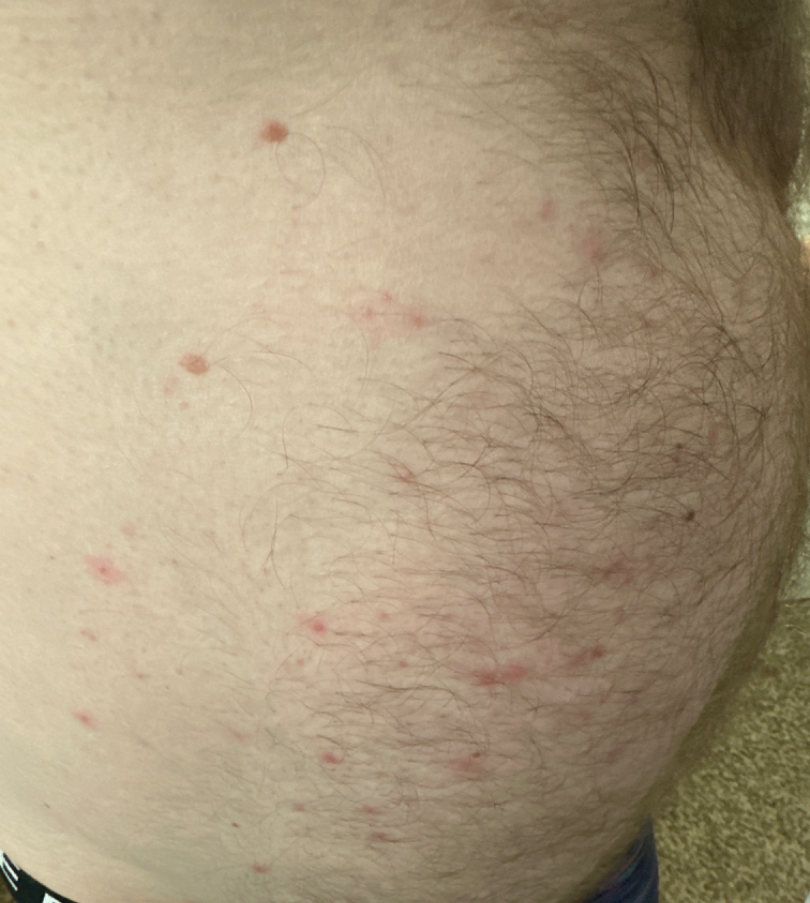Review: The skin condition could not be confidently assessed from this image. Patient information: Close-up view.